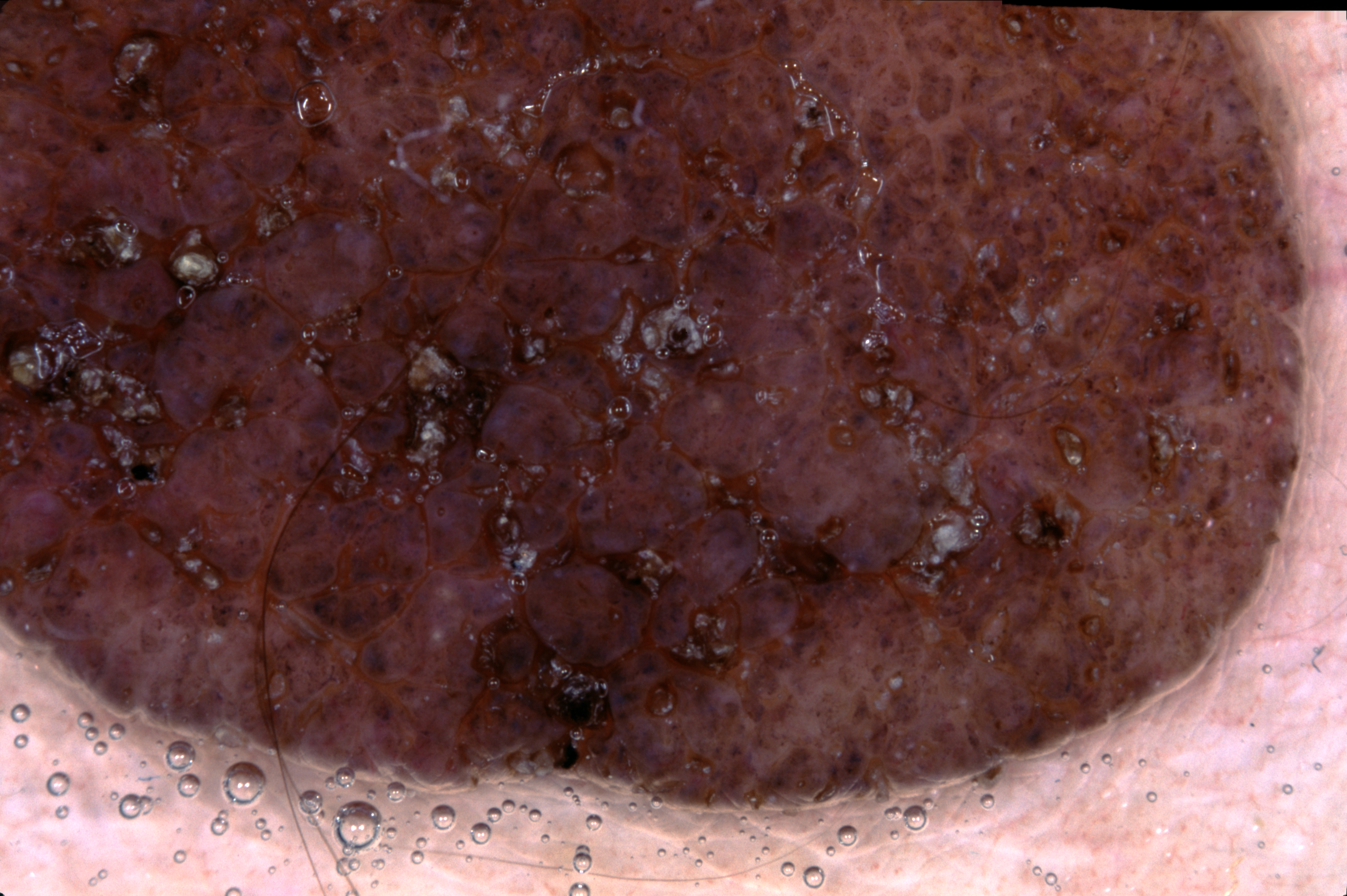Image and clinical context:
A male patient, approximately 15 years of age. A dermoscopic view of a skin lesion. The lesion extends across the full dermoscopic field. Dermoscopically, the lesion shows no pigment network, negative network, streaks, or milia-like cysts.
Conclusion:
Diagnosed as a melanocytic nevus.